A subject age 53 · a smartphone photograph of a skin lesion:
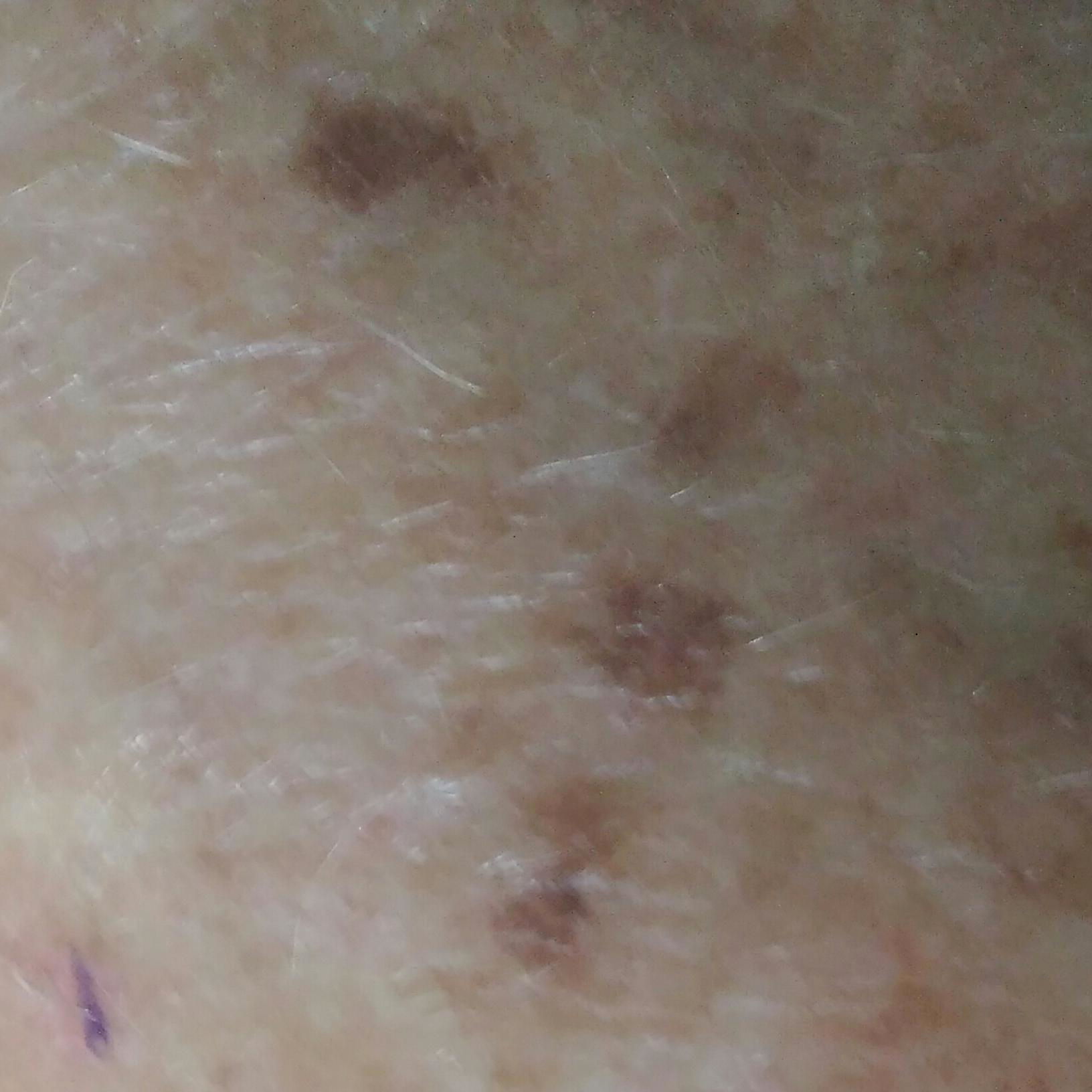The lesion was found on a hand. Clinically diagnosed as a benign skin lesion — a seborrheic keratosis.